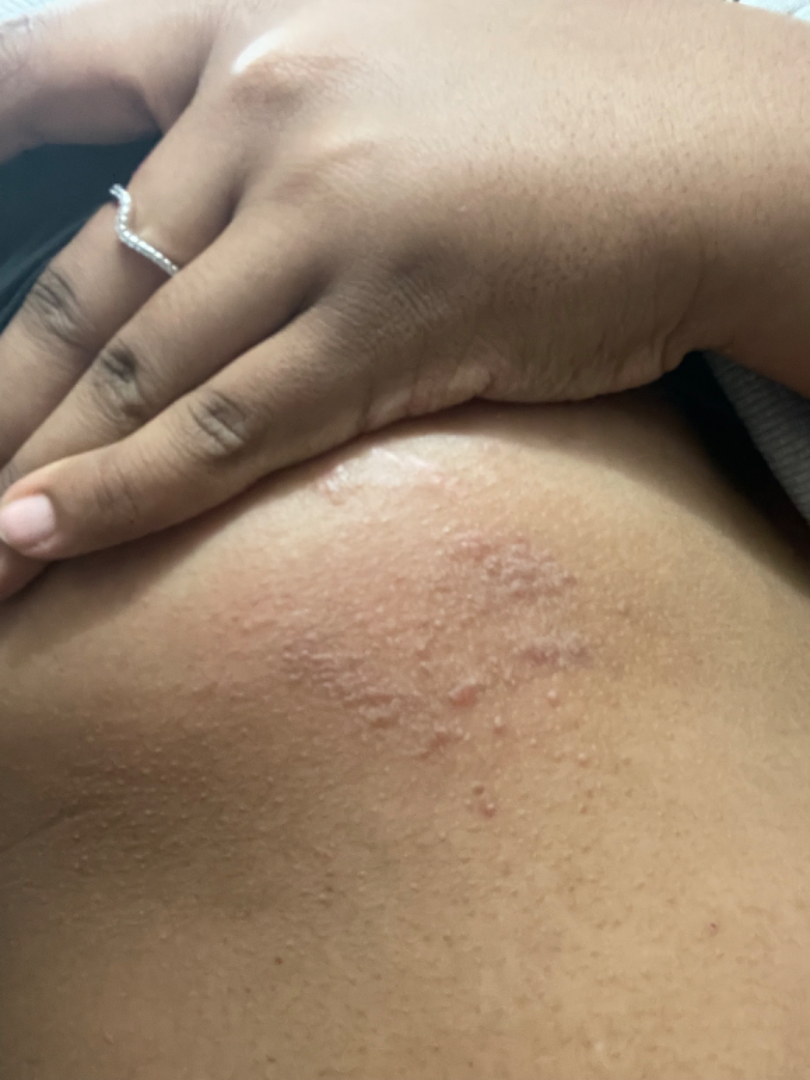Findings:
On teledermatology review, favoring Allergic Contact Dermatitis; also consider Eczema.